A dermatoscopic image of a skin lesion.
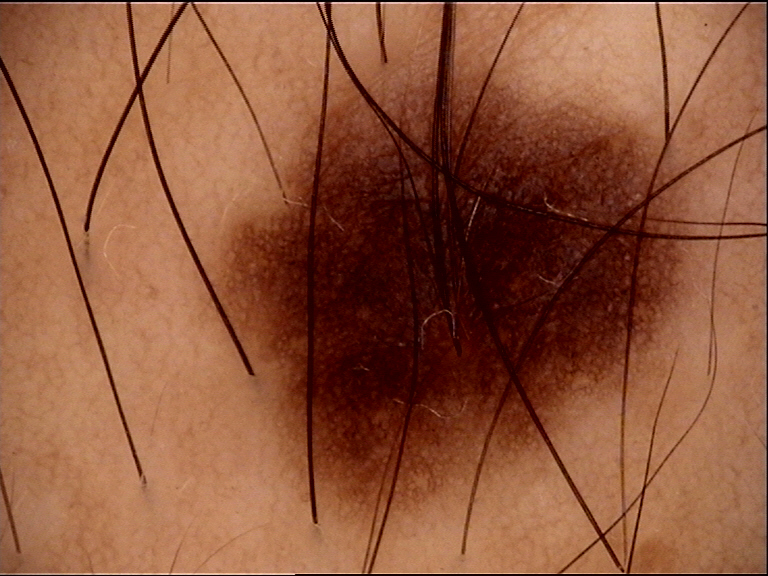Findings:
– classification: banal
– diagnostic label: junctional nevus (expert consensus)